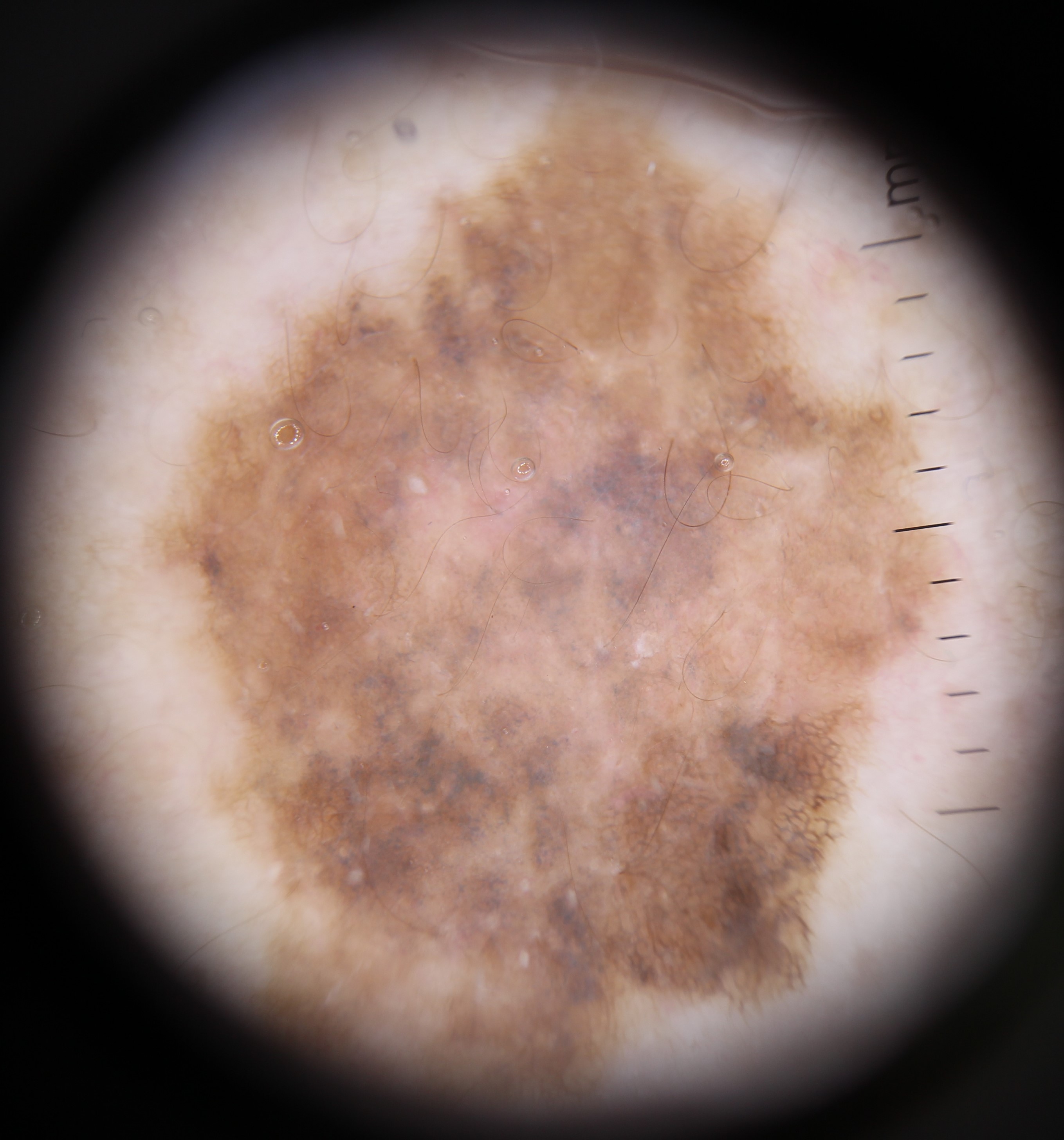Case:
– modality: dermoscopy
– diagnosis: melanoma (biopsy-proven)